A skin lesion imaged with a dermatoscope. Recorded as Fitzpatrick phototype II. A female patient approximately 50 years of age.
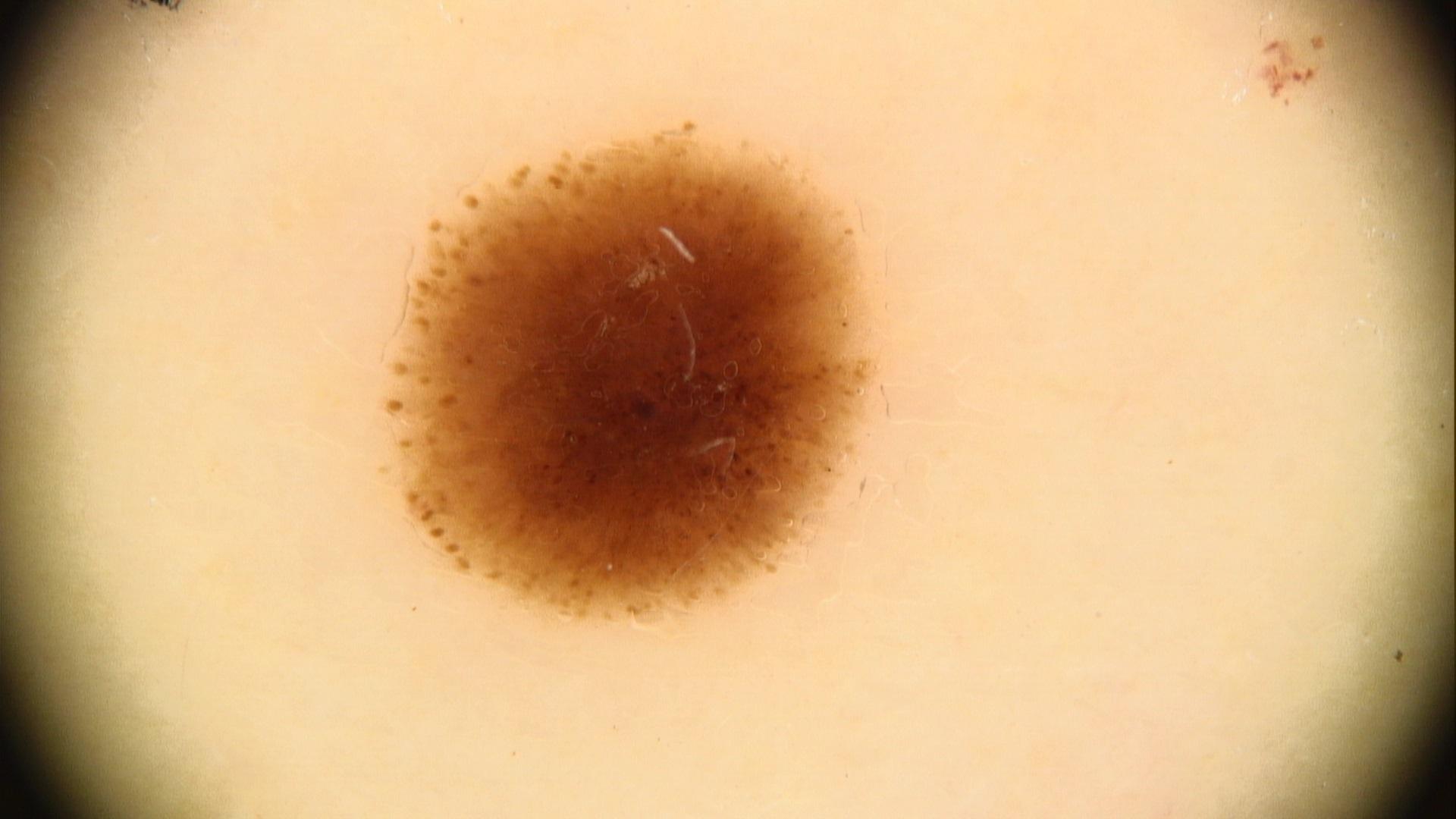Findings:
The lesion was found on the trunk (the anterior trunk).
Diagnosis:
Histopathologically confirmed as a lesion of melanocytic lineage — a nevus.